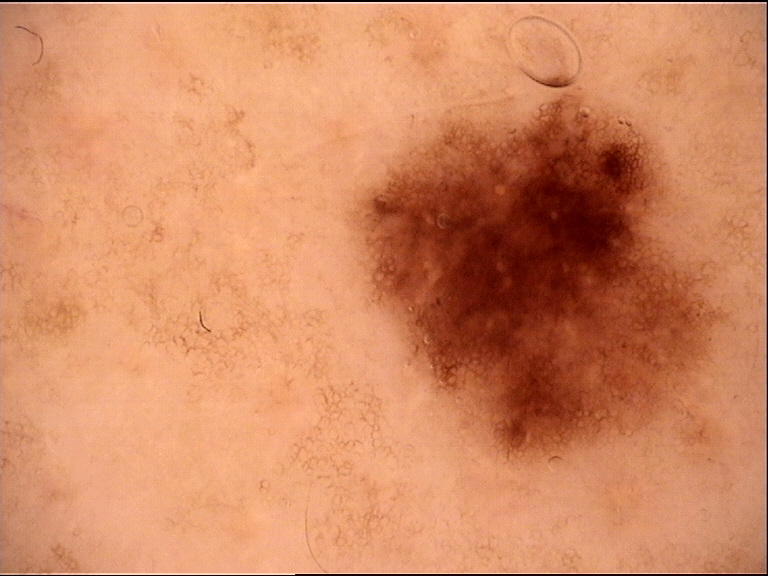imaging: dermoscopy | diagnostic label: dysplastic junctional nevus (expert consensus).